A dermatoscopic image of a skin lesion.
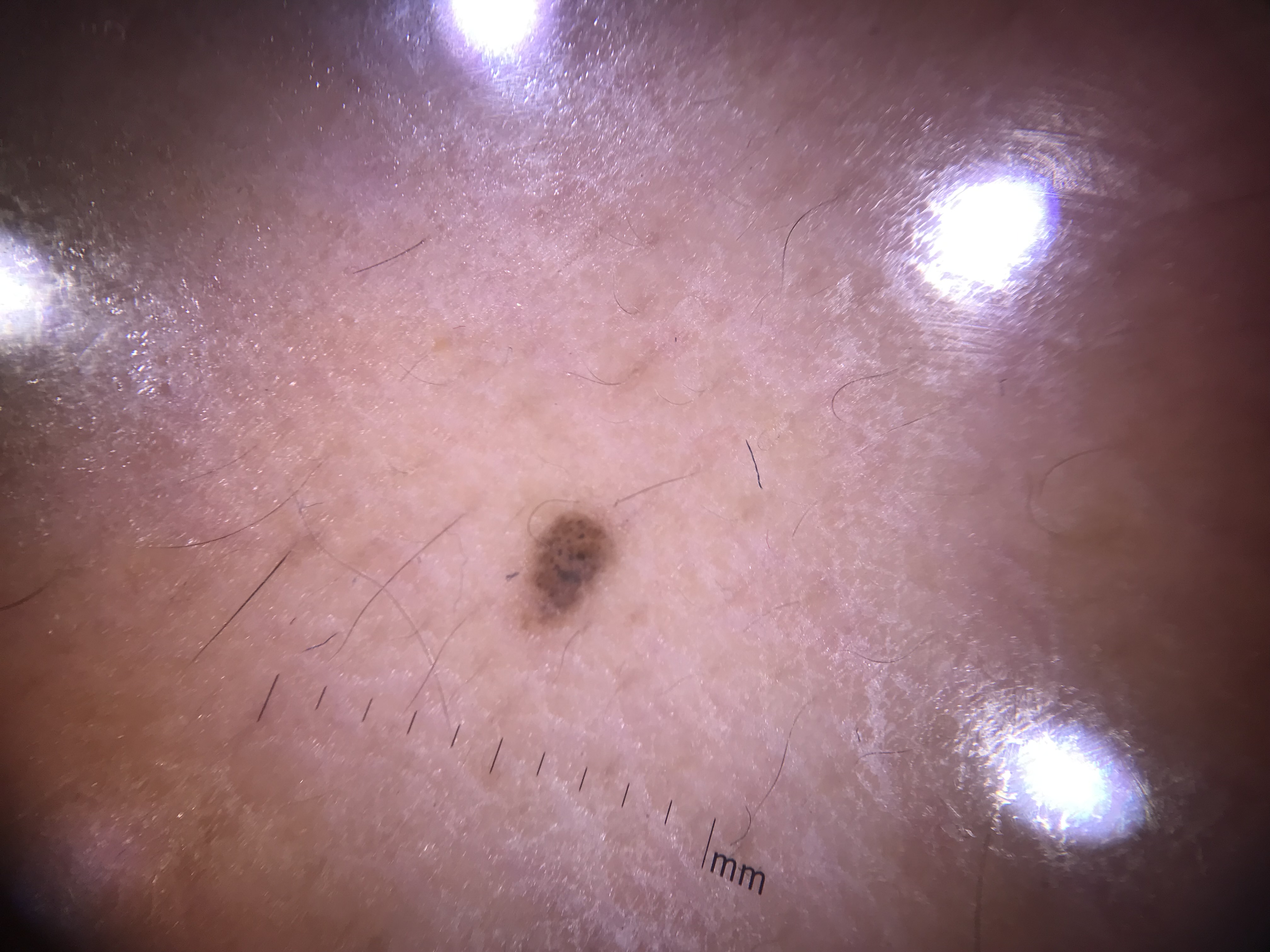Q: What is the diagnosis?
A: junctional nevus (expert consensus)